A dermoscopic photograph of a skin lesion.
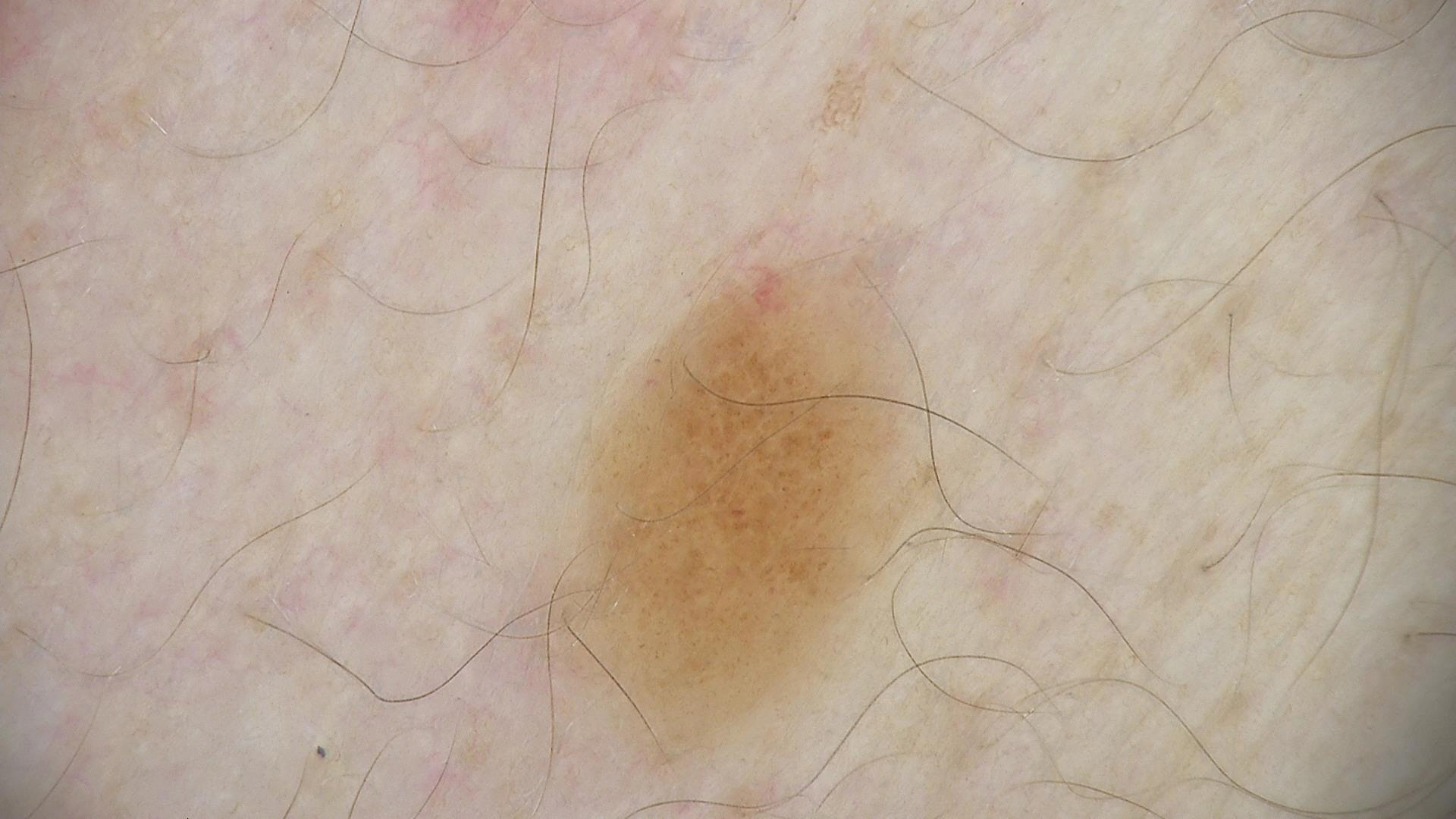The architecture is that of a banal lesion.
The diagnosis was a junctional nevus.